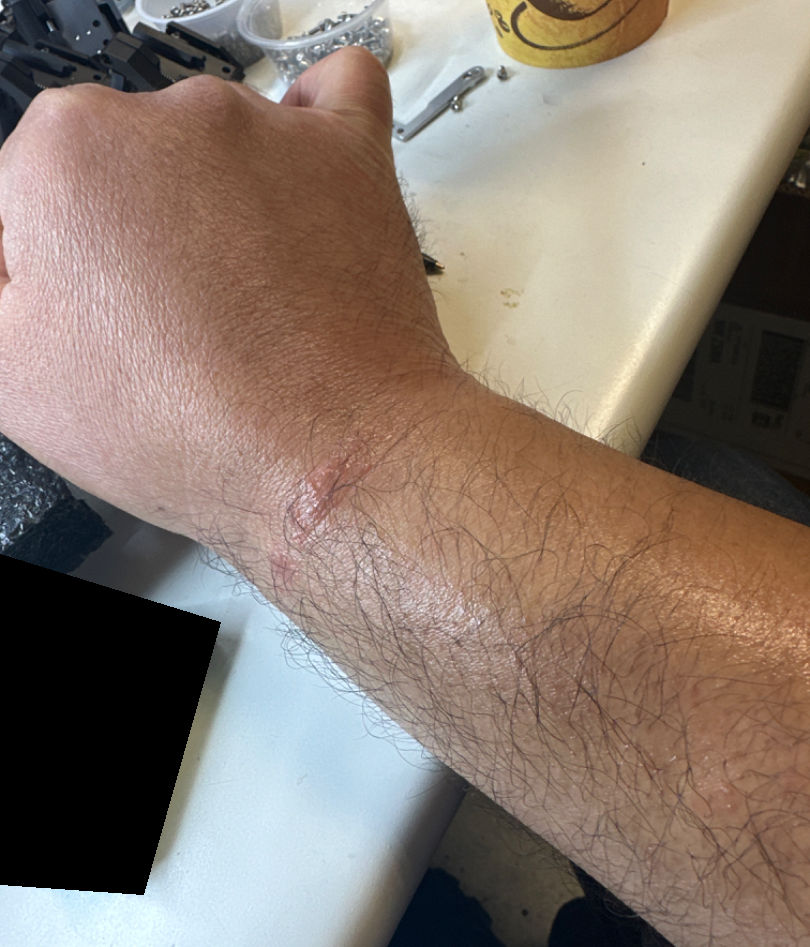Q: How was the photo taken?
A: at an angle
Q: What conditions are considered?
A: Scar Condition (33%); Allergic Contact Dermatitis (33%); Abrasion, scrape, or scab (33%)